A clinical close-up photograph of a skin lesion; a male patient age 63.
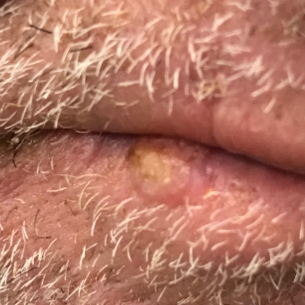• anatomic site · a lip
• symptoms · change in appearance, growth, elevation / no itching, no bleeding
• diagnosis · squamous cell carcinoma (biopsy-proven)